The condition has been present for about one day; the lesion is described as flat; the photograph was taken at an angle; symptoms reported: enlargement and itching; the affected area is the arm and leg; the patient considered this a rash; the patient is a female aged 30–39:
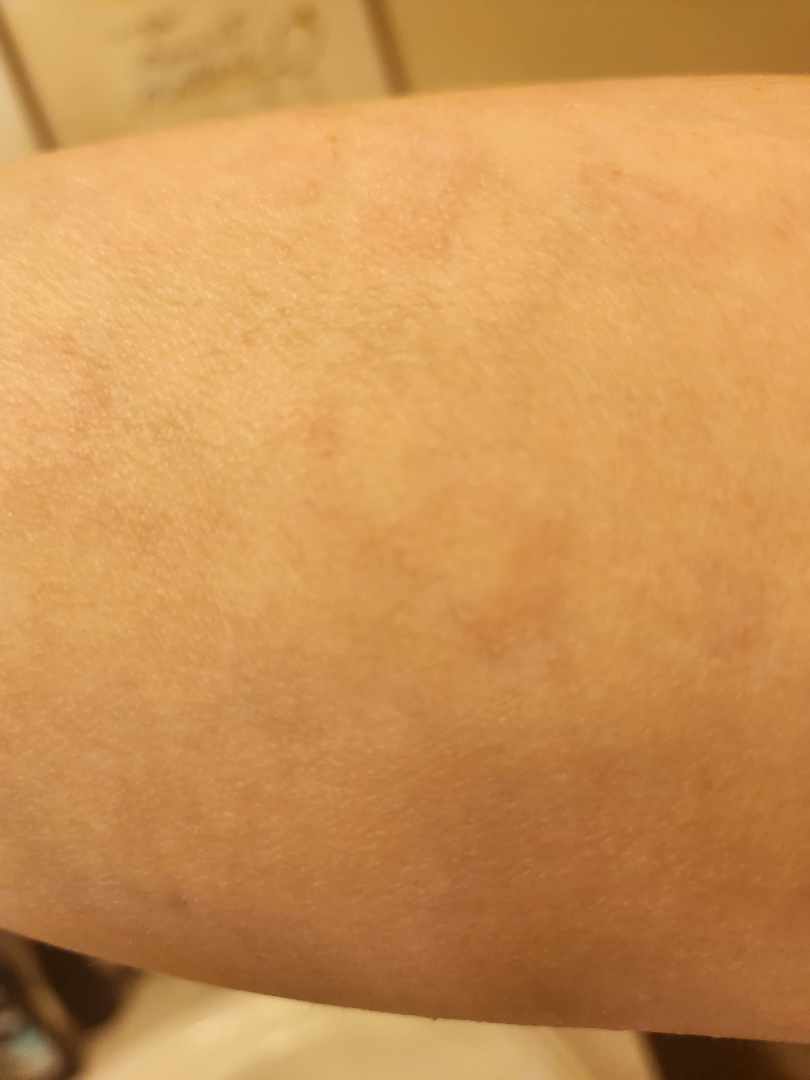assessment: ungradable on photographic review